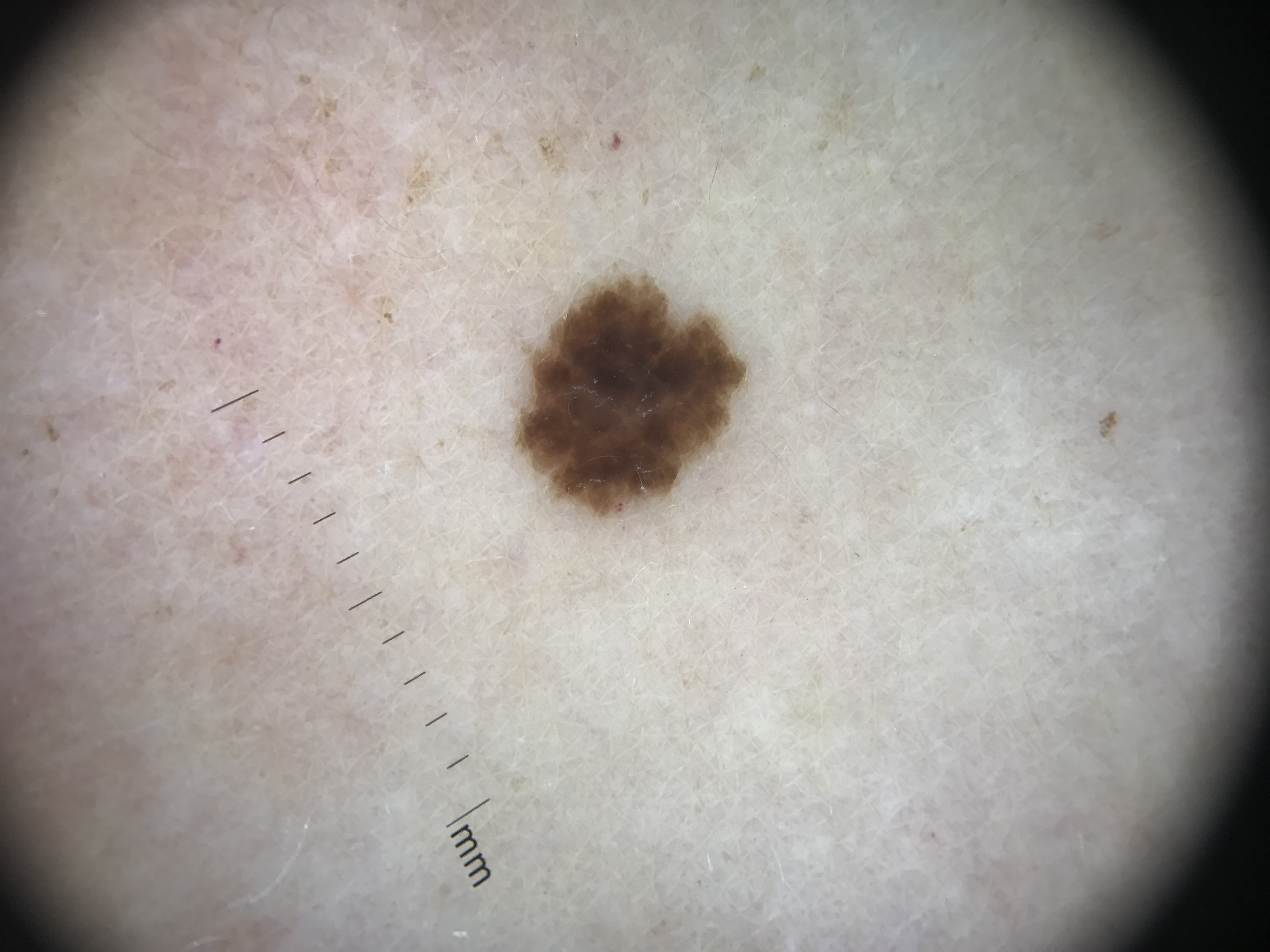modality: dermatoscopy | label: dysplastic junctional nevus (expert consensus).